The patient is a male roughly 50 years of age, a dermatoscopic image of a skin lesion — 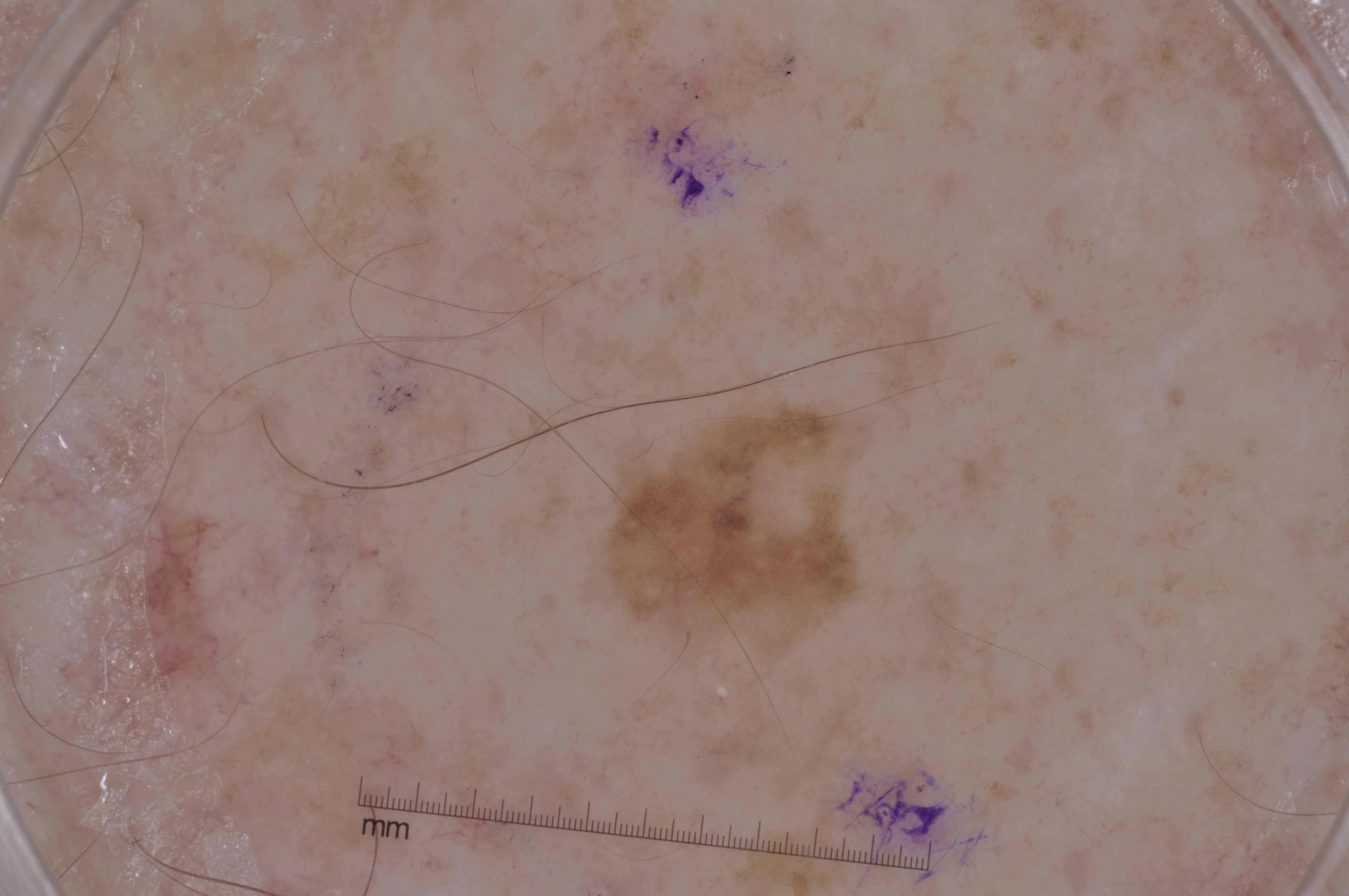{"dermoscopic_features": {"present": ["pigment network"], "absent": ["milia-like cysts", "negative network", "streaks"]}, "lesion_location": {"bbox_xyxy": [601, 413, 854, 637]}, "diagnosis": {"name": "melanocytic nevus", "malignancy": "benign", "lineage": "melanocytic", "provenance": "clinical"}}